The patient indicates the lesion is raised or bumpy and fluid-filled. Self-categorized by the patient as a rash. The condition has been present for about one day. Reported lesion symptoms include bothersome appearance. Male subject, age 40–49. This image was taken at an angle: 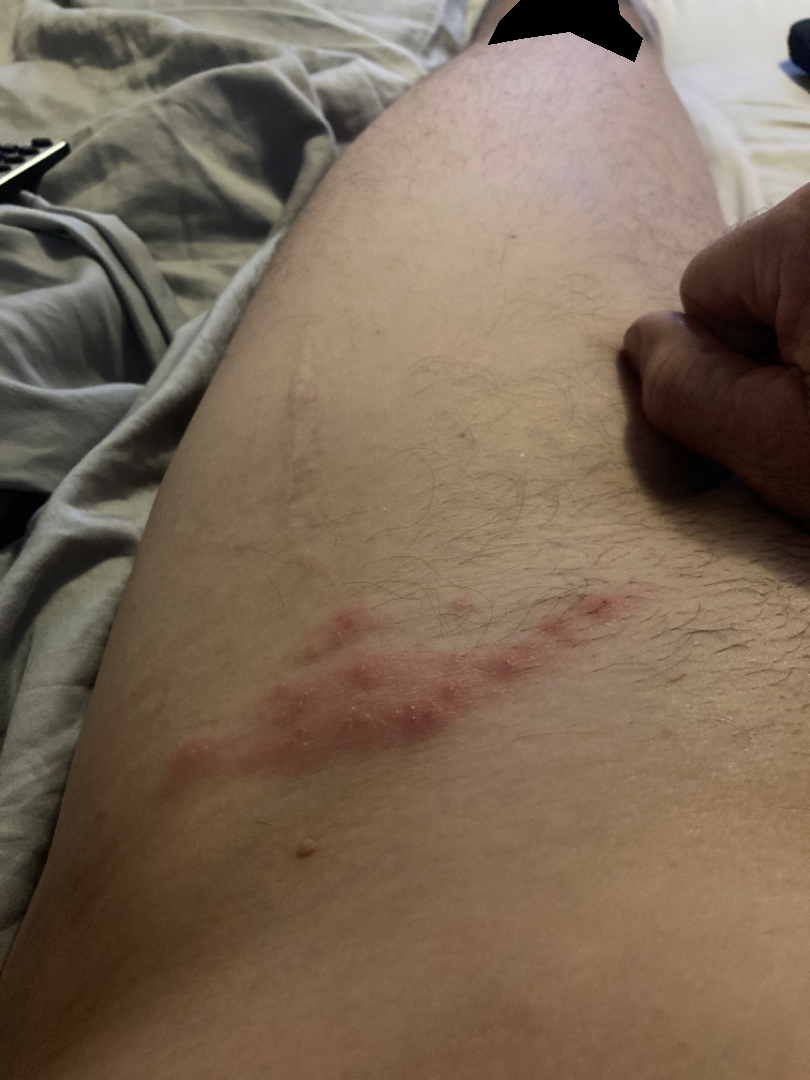Consistent with Herpes Zoster.